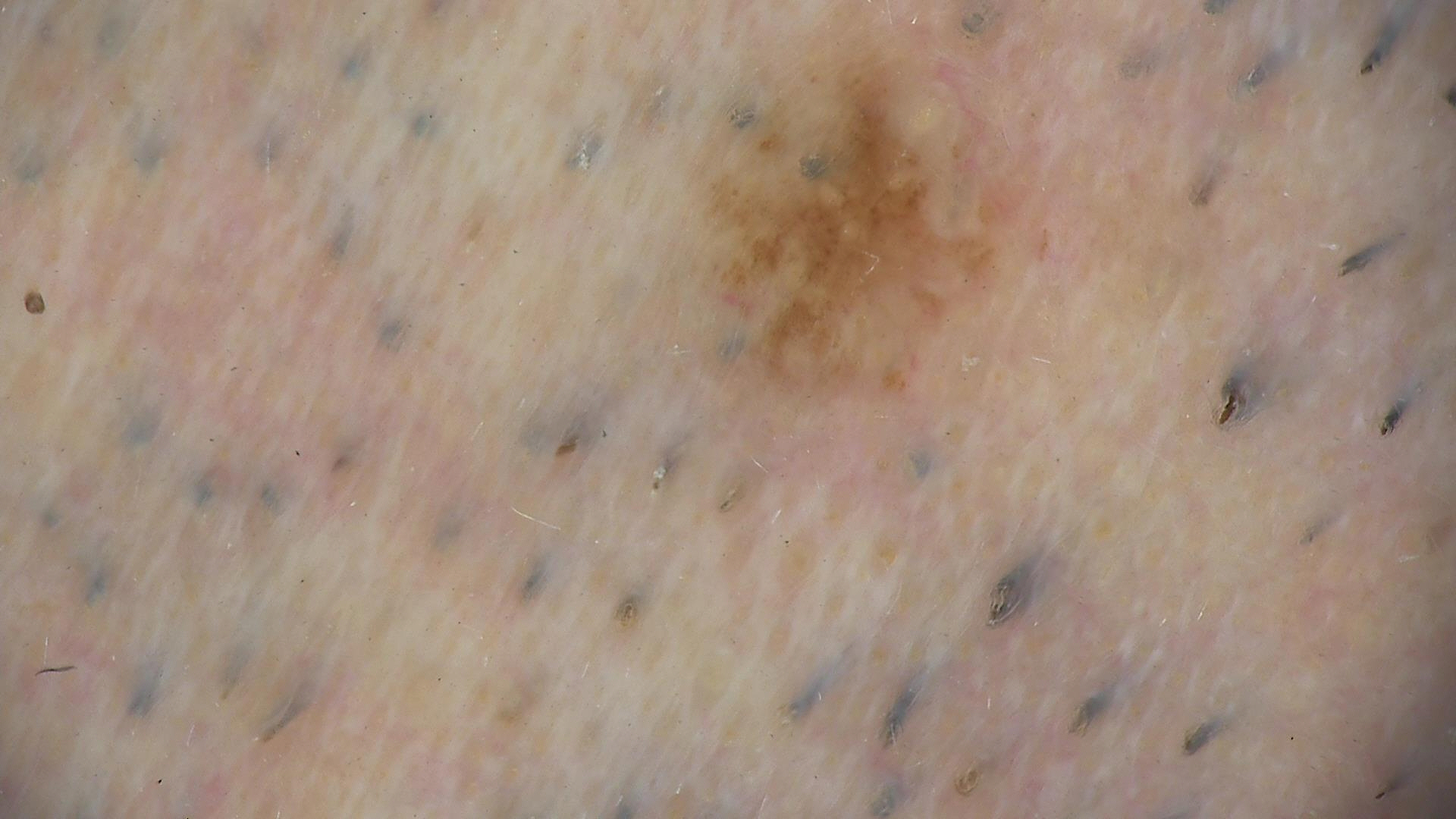<case>
  <image>dermatoscopy</image>
  <diagnosis>
    <name>Miescher nevus</name>
    <code>mcb</code>
    <malignancy>benign</malignancy>
    <super_class>melanocytic</super_class>
    <confirmation>expert consensus</confirmation>
  </diagnosis>
</case>